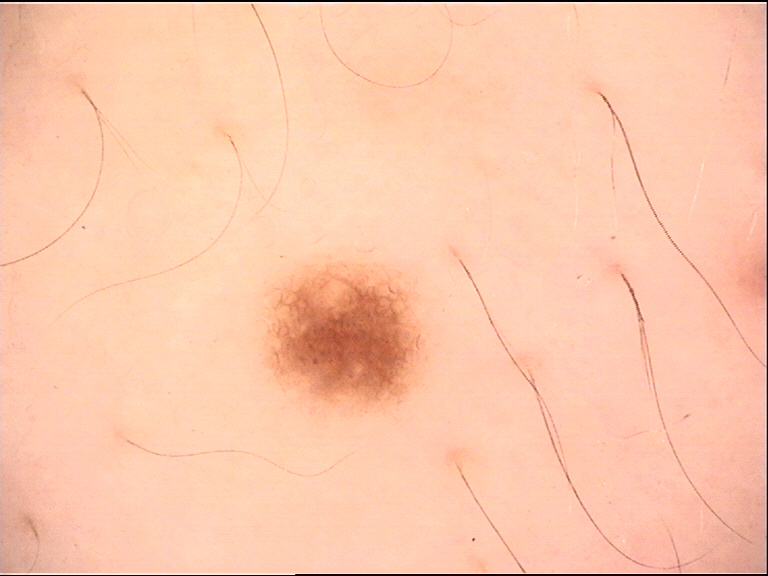Q: What kind of image is this?
A: dermatoscopy
Q: What was the diagnostic impression?
A: dysplastic junctional nevus (expert consensus)